A dermoscopy image of a single skin lesion: 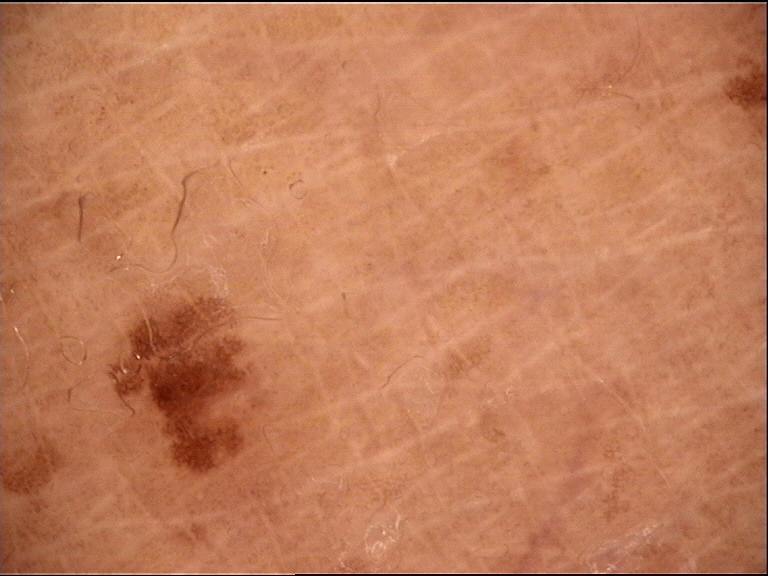The diagnosis was a dysplastic junctional nevus.